This is a close-up image.
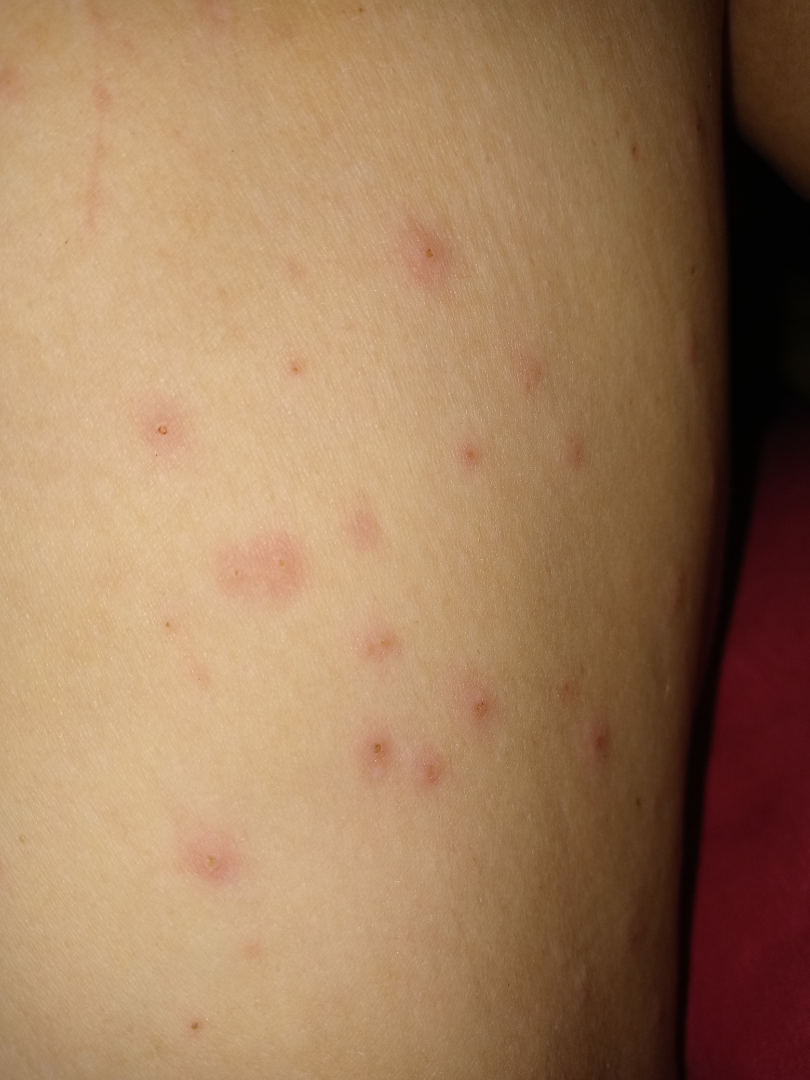Hypersensitivity (leading); Insect Bite (possible).